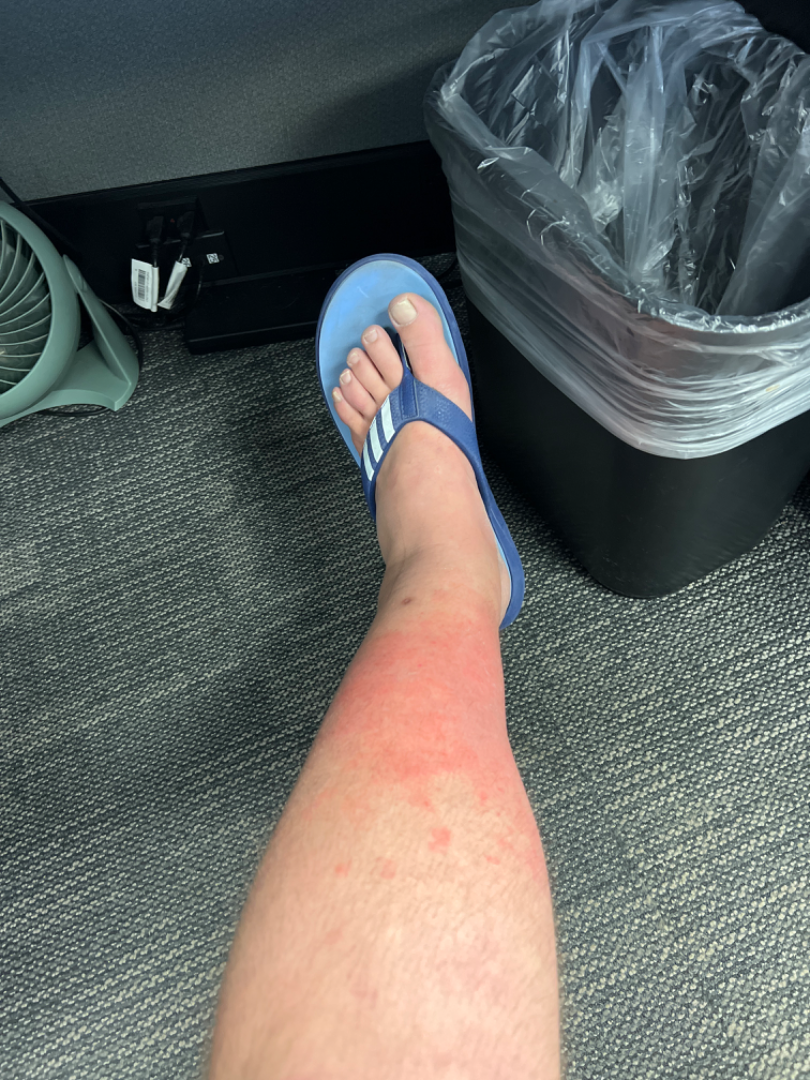diagnostic considerations=the impression is Stasis Dermatitis.